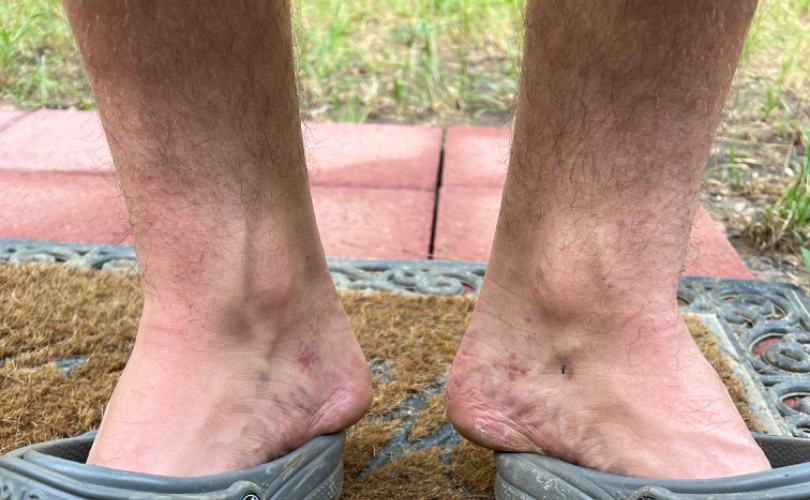  body_site:
    - top or side of the foot
    - sole of the foot
  shot_type: at a distance
  patient_category: a rash
  patient: male, age 18–29
  symptoms: enlargement
  duration: more than one year
  differential:
    leading:
      - Lichen planus/lichenoid eruption
    considered:
      - Insect Bite
      - Allergic Contact Dermatitis